A dermoscopy image of a single skin lesion.
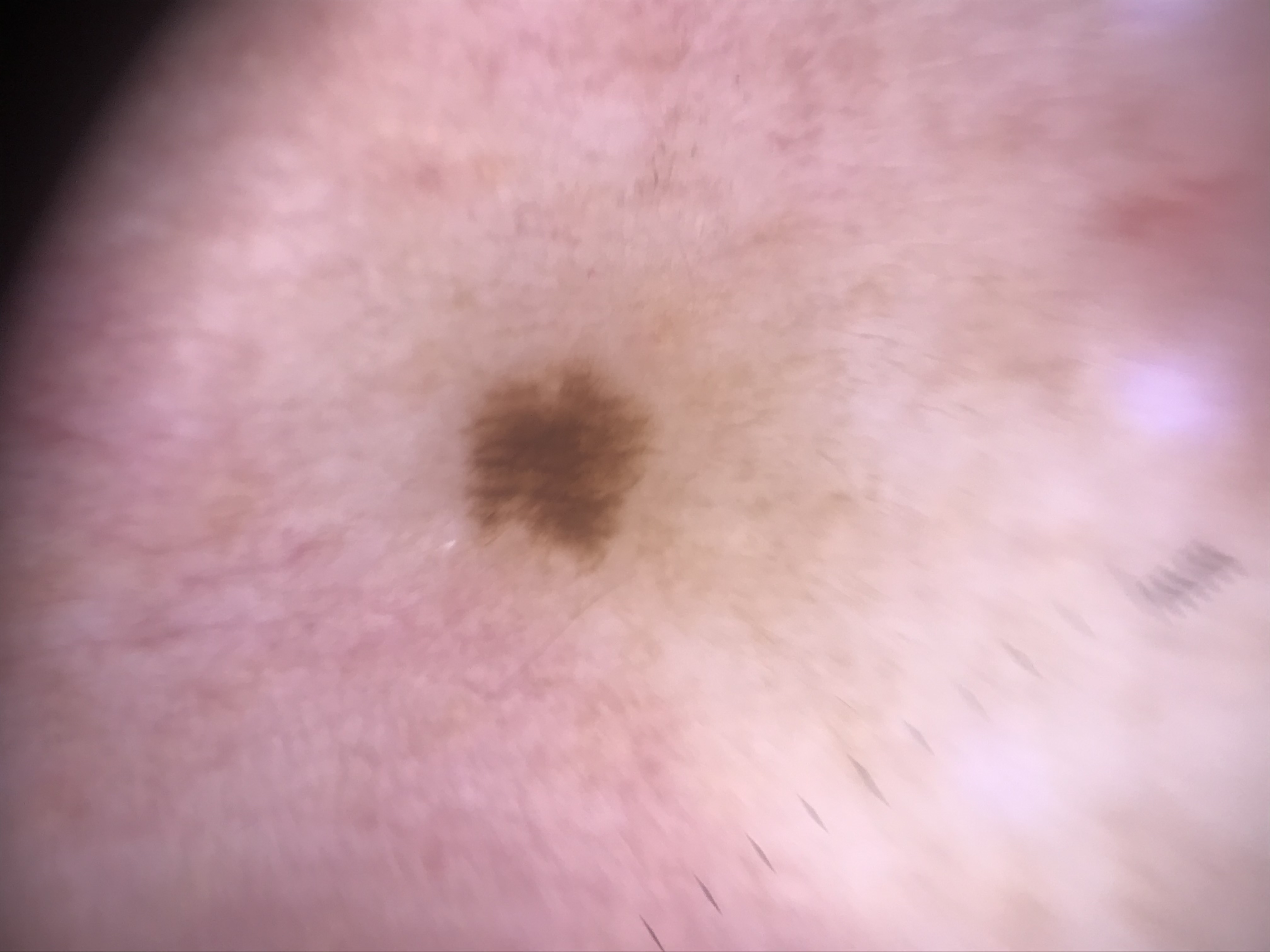{
  "diagnosis": {
    "name": "junctional nevus",
    "code": "jb",
    "malignancy": "benign",
    "super_class": "melanocytic",
    "confirmation": "expert consensus"
  }
}